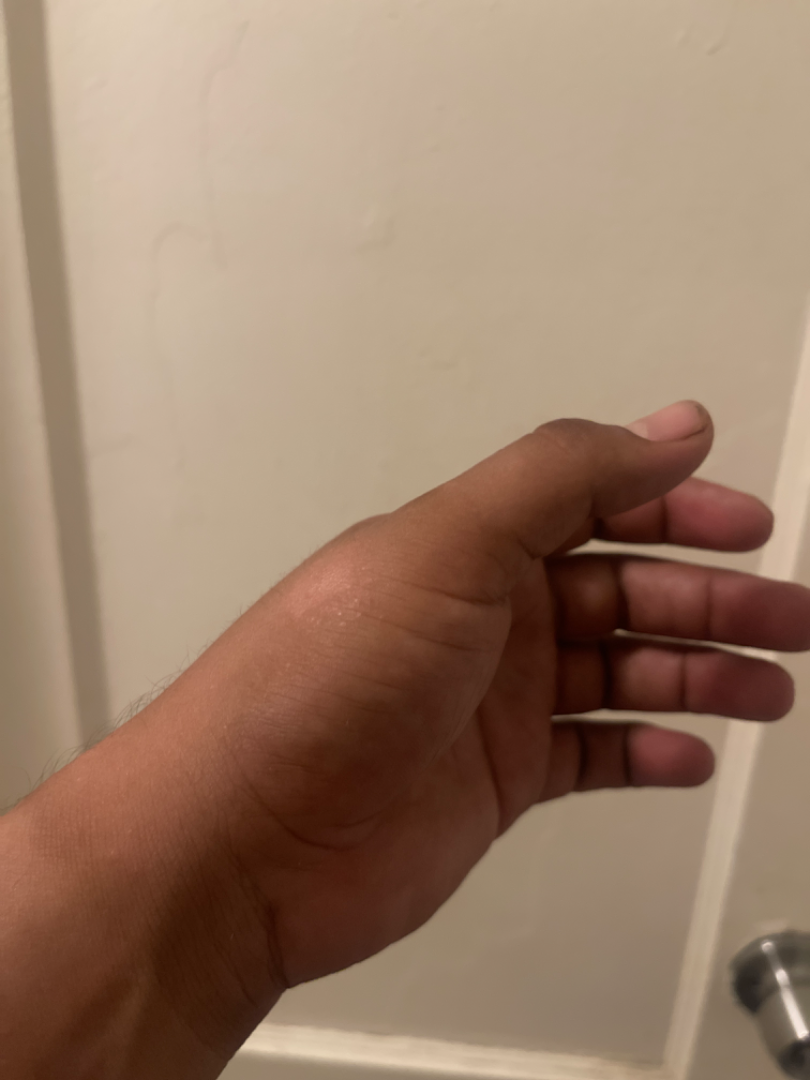The reviewing dermatologist was unable to assign a differential diagnosis from the image.